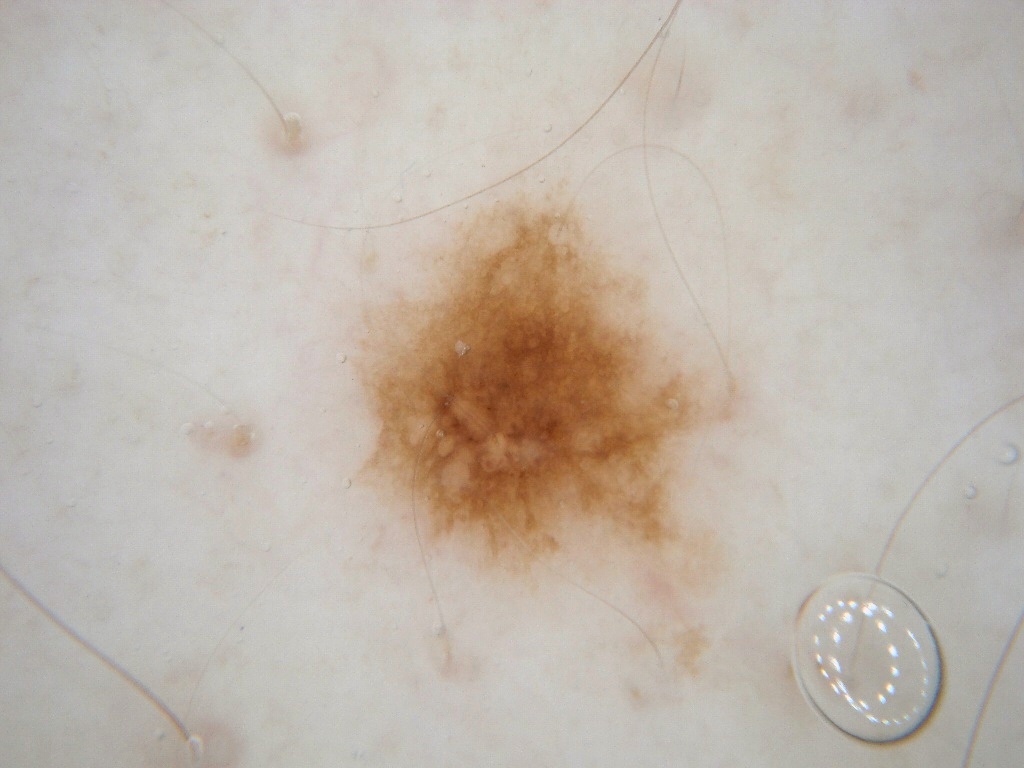Case summary:
• image type — dermoscopic image
• patient — male, in their mid- to late 50s
• features — pigment network; absent: milia-like cysts, globules, streaks, and negative network
• size — moderate
• location — (316, 168, 750, 593)
• assessment — a melanocytic nevus, a benign lesion